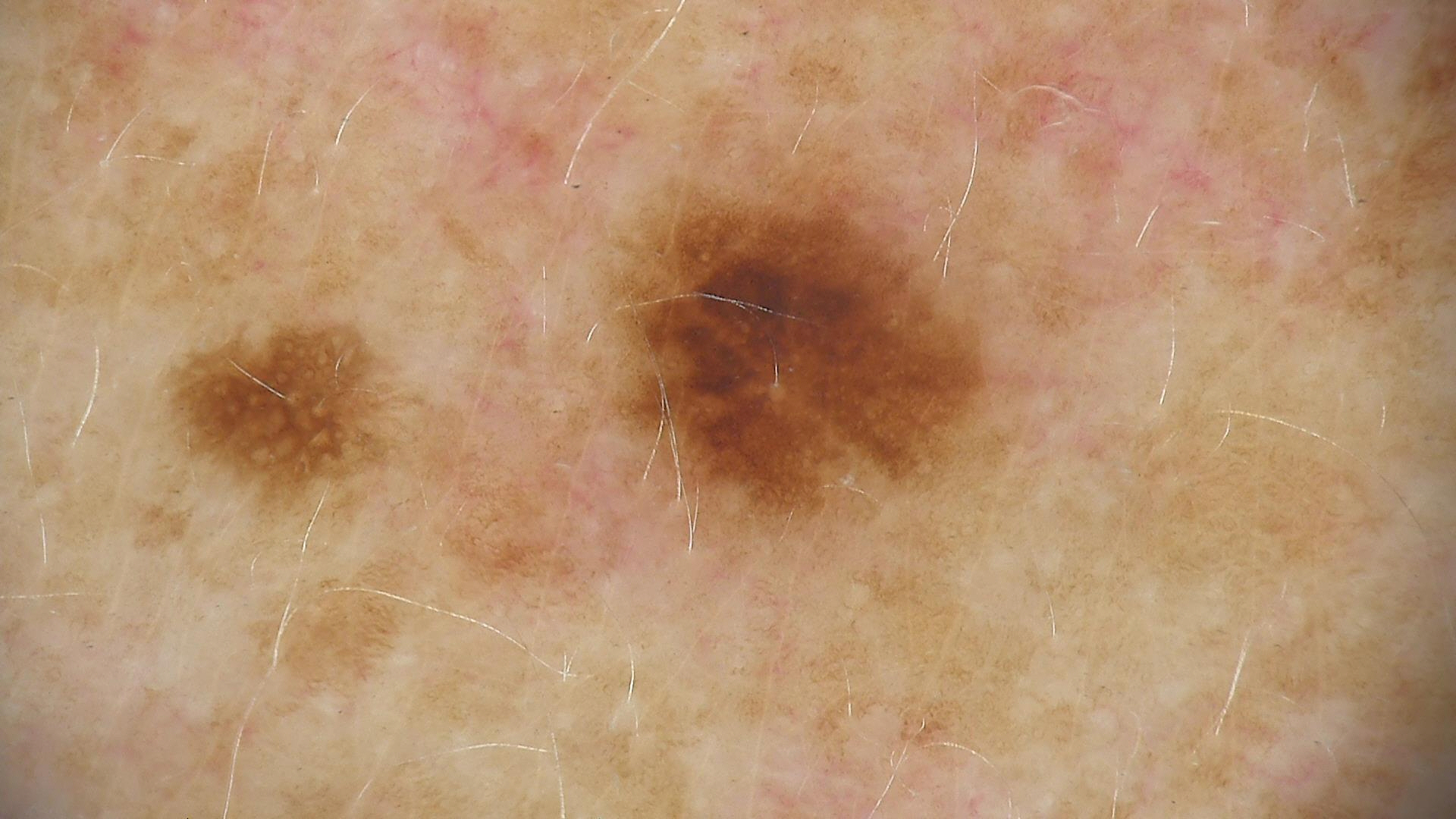Impression:
Classified as a dysplastic junctional nevus.